Symptoms reported: itching and enlargement · the patient is 40–49, female · the contributor notes the condition has been present for one to four weeks · this is a close-up image · the lesion is described as rough or flaky and raised or bumpy · the patient described the issue as a rash:
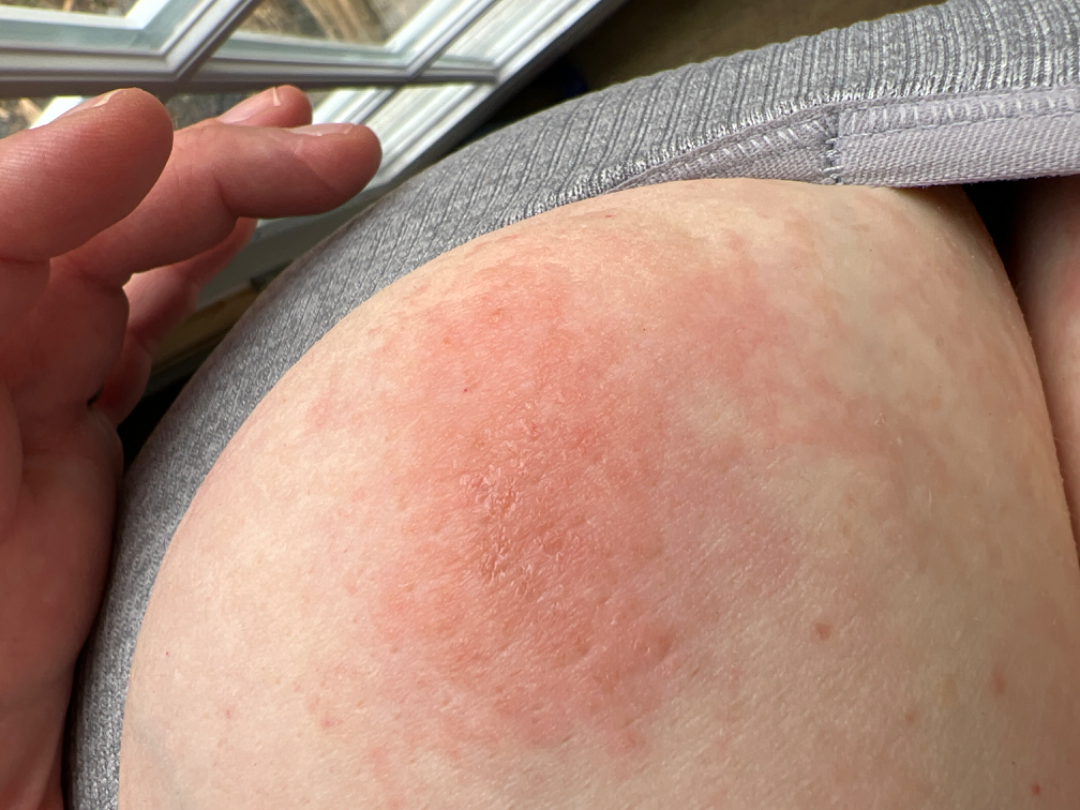Assessment:
On teledermatology review, Eczema and Allergic Contact Dermatitis were each considered, in no particular order; a remote consideration is Psoriasis.